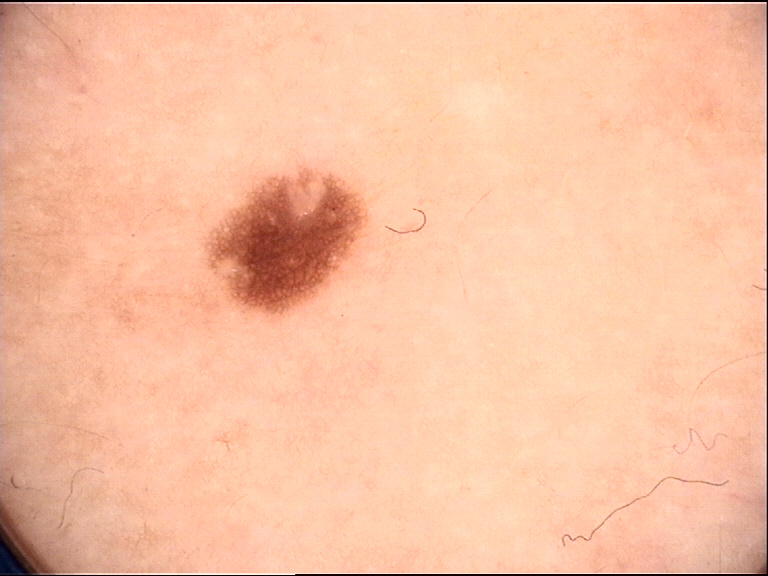Case:
- image · dermatoscopy
- class · dysplastic junctional nevus (expert consensus)